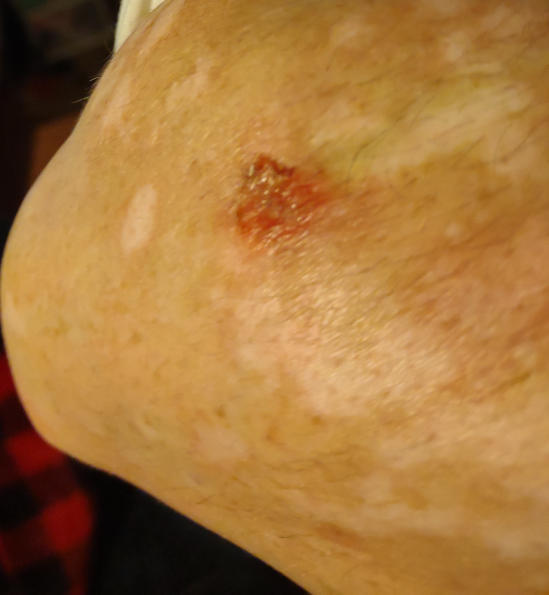dermatologist impression — the favored diagnosis is Impetigo.